A clinical photograph showing a skin lesion; recorded as Fitzpatrick skin type I: 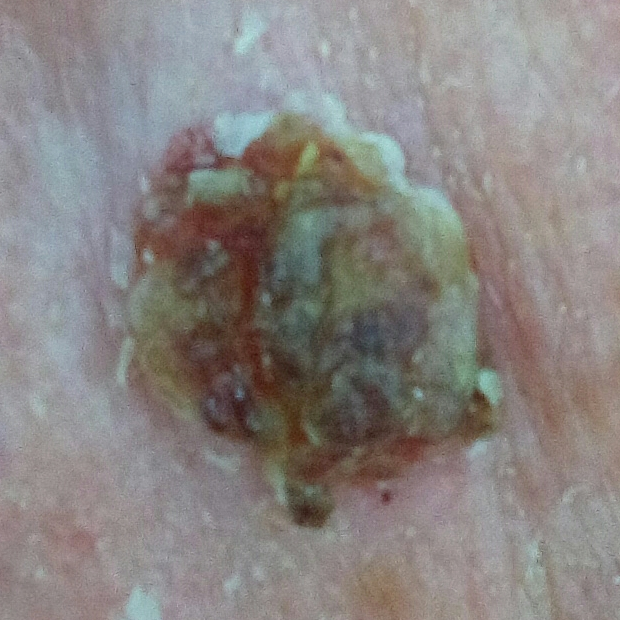Patient and lesion:
The lesion is on an ear. The lesion measures approximately 11 × 11 mm. Per patient report, the lesion itches, hurts, has bled, and is elevated.
Diagnosis:
Histopathology confirmed a basal cell carcinoma.